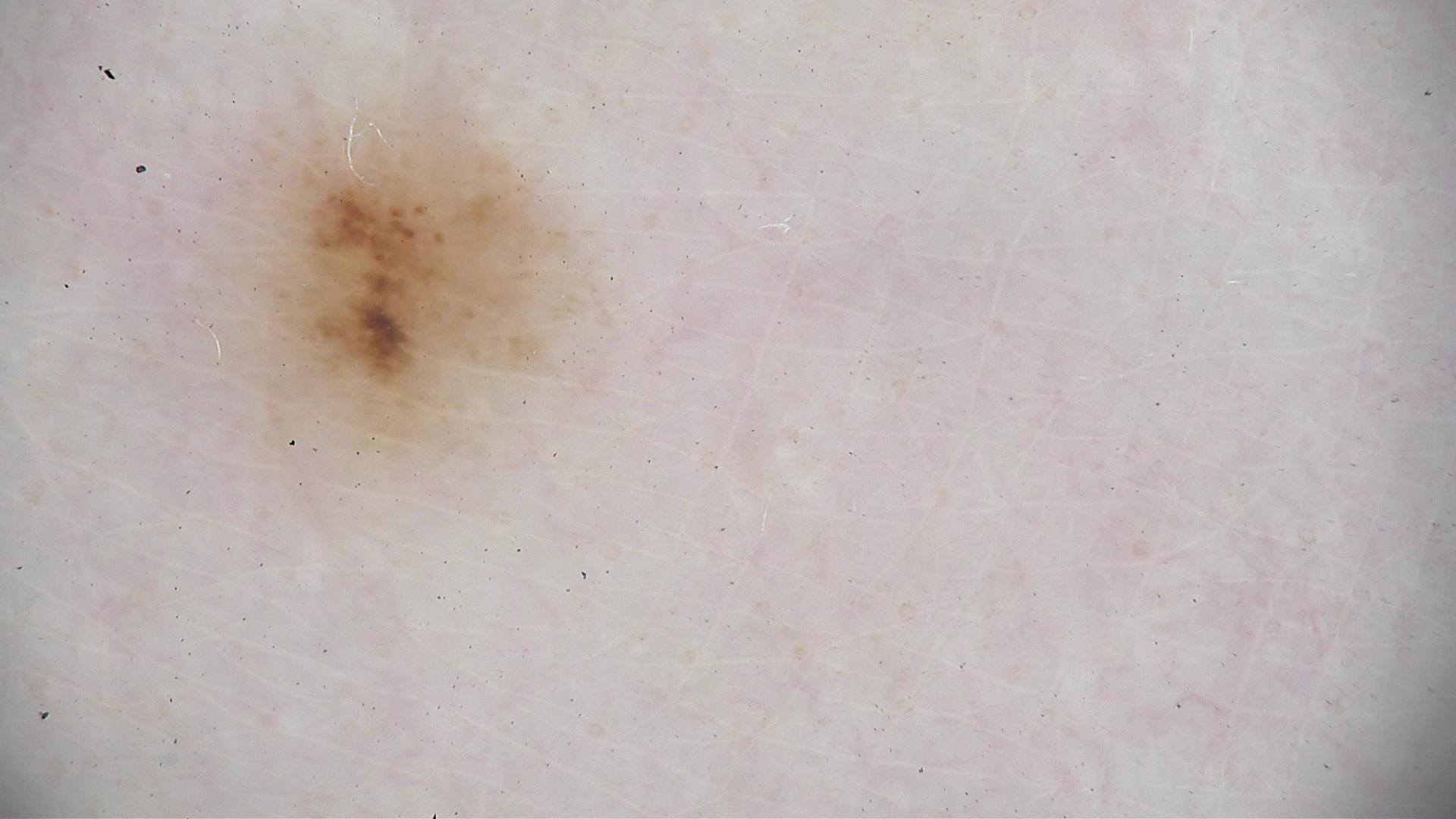A dermoscopic close-up of a skin lesion. The diagnostic label was a benign lesion — an acral dysplastic junctional nevus.